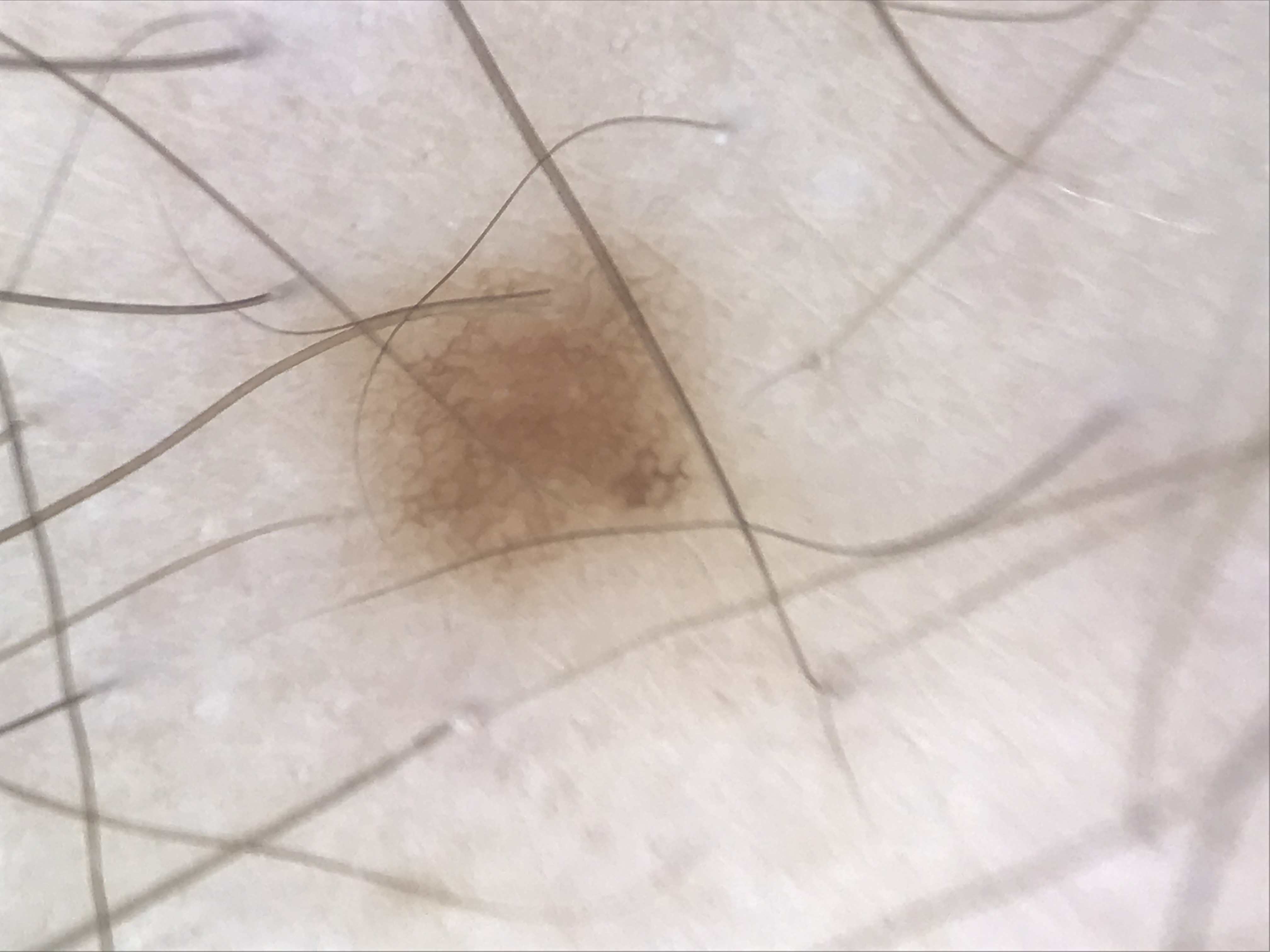Q: What kind of image is this?
A: dermatoscopy
Q: What is the lesion category?
A: banal
Q: What was the diagnostic impression?
A: junctional nevus (expert consensus)